A dermoscopy image of a single skin lesion: 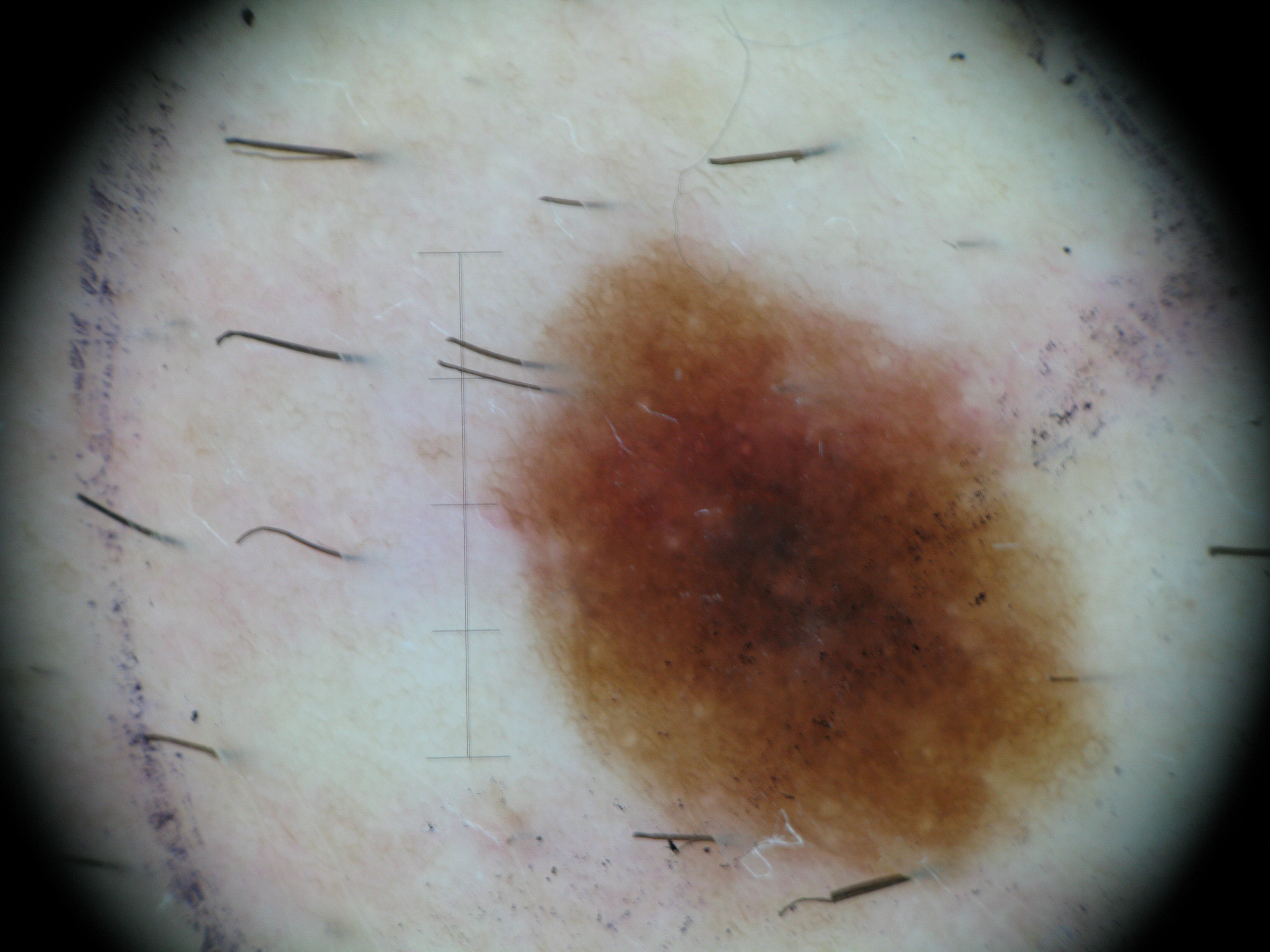label — dysplastic compound nevus (expert consensus).